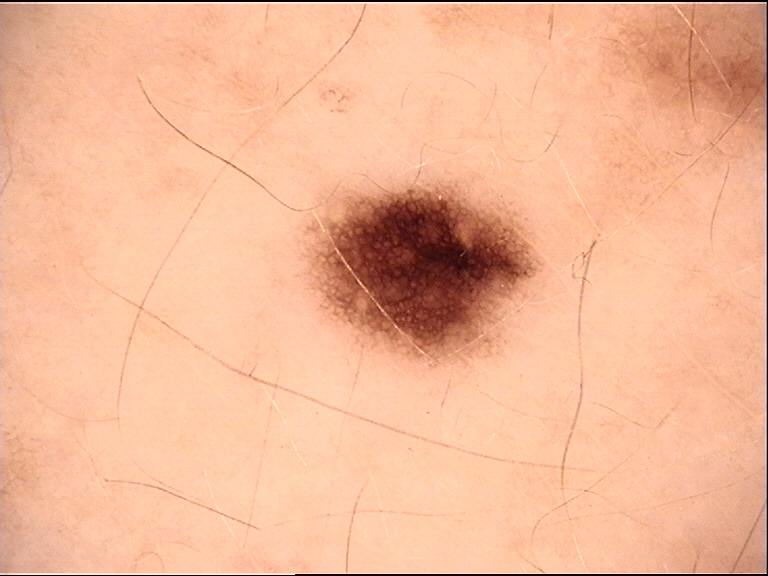Summary:
A skin lesion imaged with a dermatoscope.
Conclusion:
The diagnostic label was a benign lesion — a dysplastic junctional nevus.